Dermoscopy of a skin lesion; a female subject aged 84: 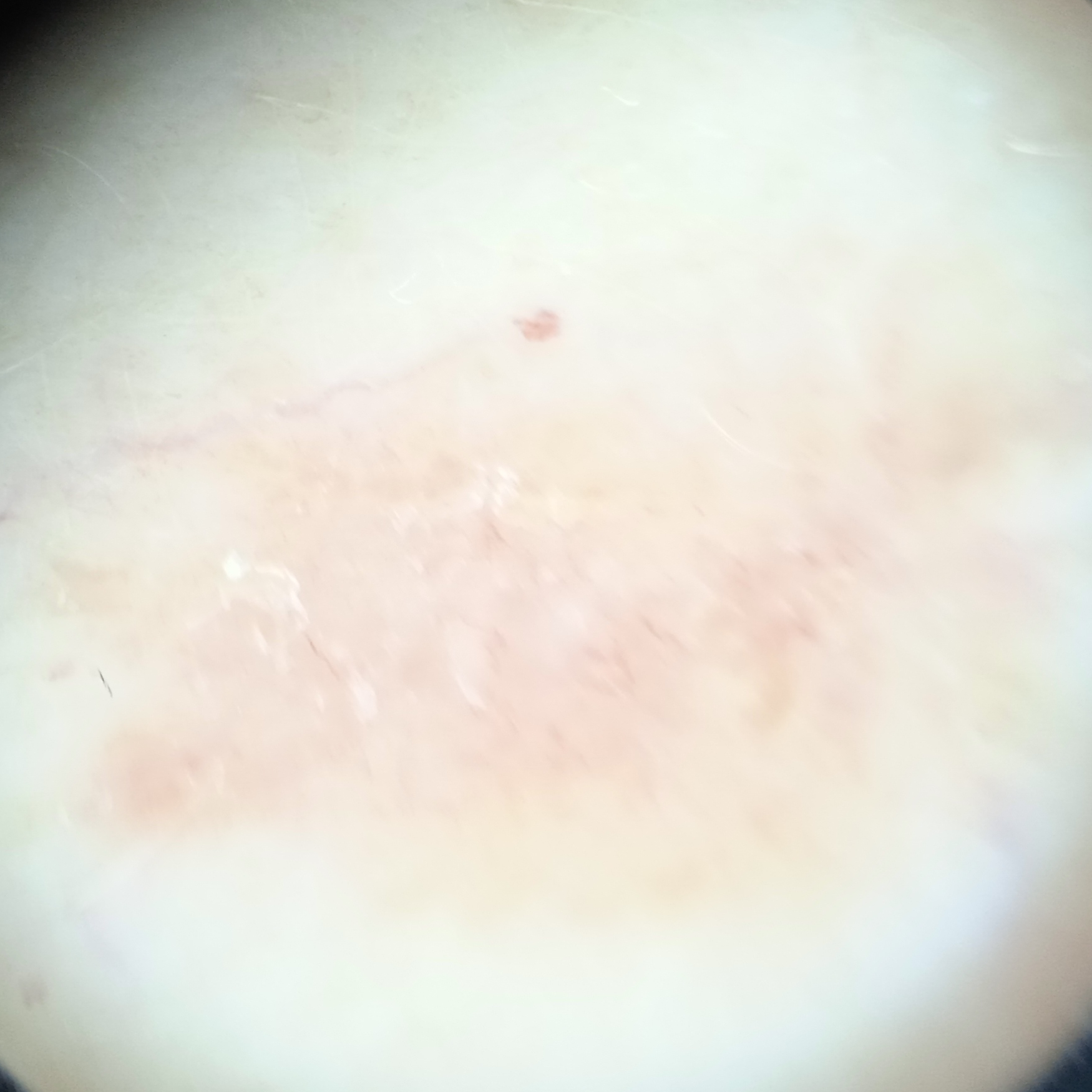Located on the torso.
The lesion measures approximately 12.5 mm.
The biopsy diagnosis was a basal cell carcinoma, following a punch biopsy, with a measured tumor thickness of 2 mm.